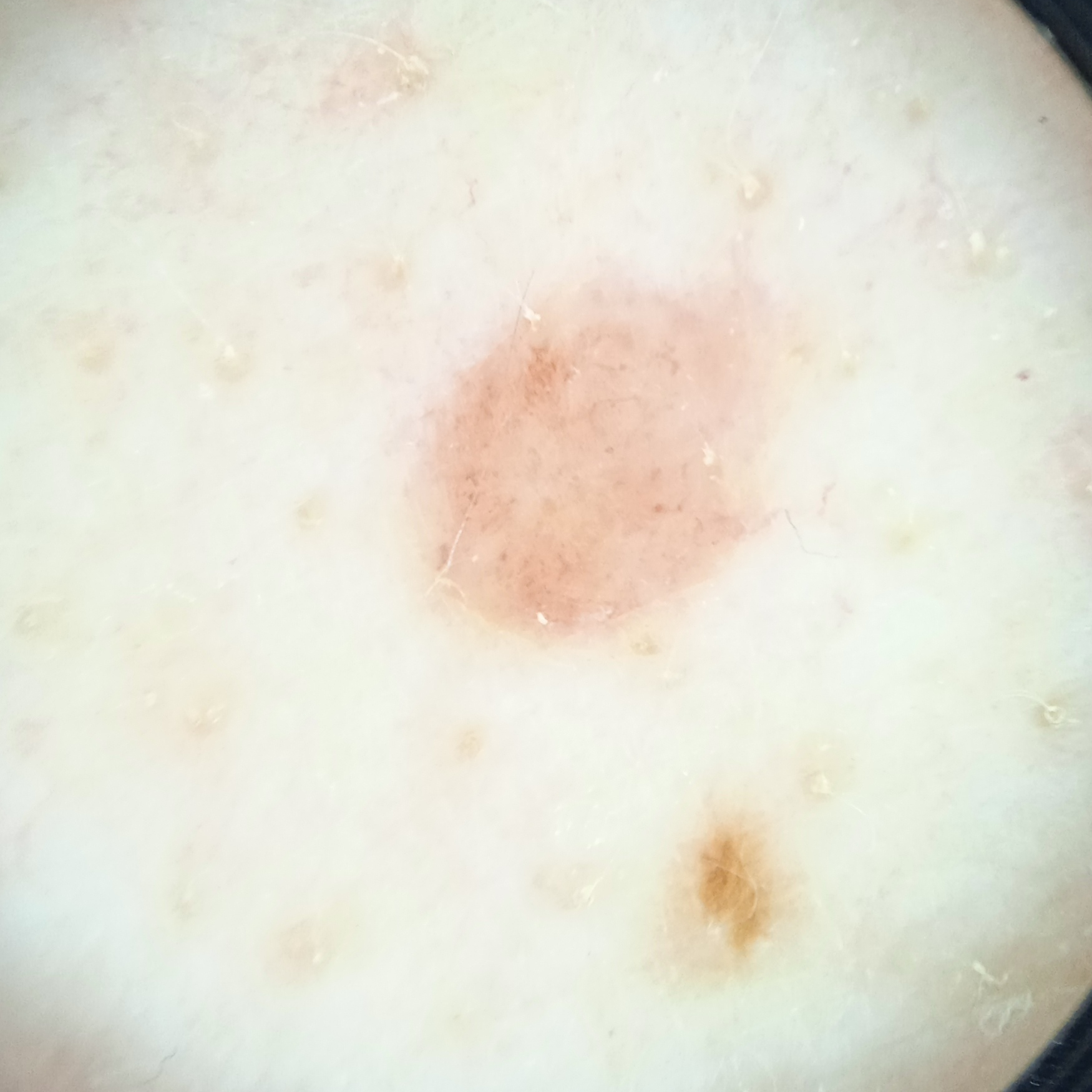Findings:
On a questionnaire the patient reported immunosuppression, a personal history of skin cancer, a family history of skin cancer, no personal history of cancer, and no prior organ transplant. The patient says their skin reddens painfully with sun exposure. A dermoscopic image of a skin lesion. Collected as part of a research study, without a referral diagnosis. A male patient 65 years of age. The patient describes having numerous moles. The lesion involves the back. The lesion measures approximately 4.4 mm.
Impression:
The lesion was assessed as a melanocytic nevus.